A dermoscopic close-up of a skin lesion. The subject is a male aged 28-32.
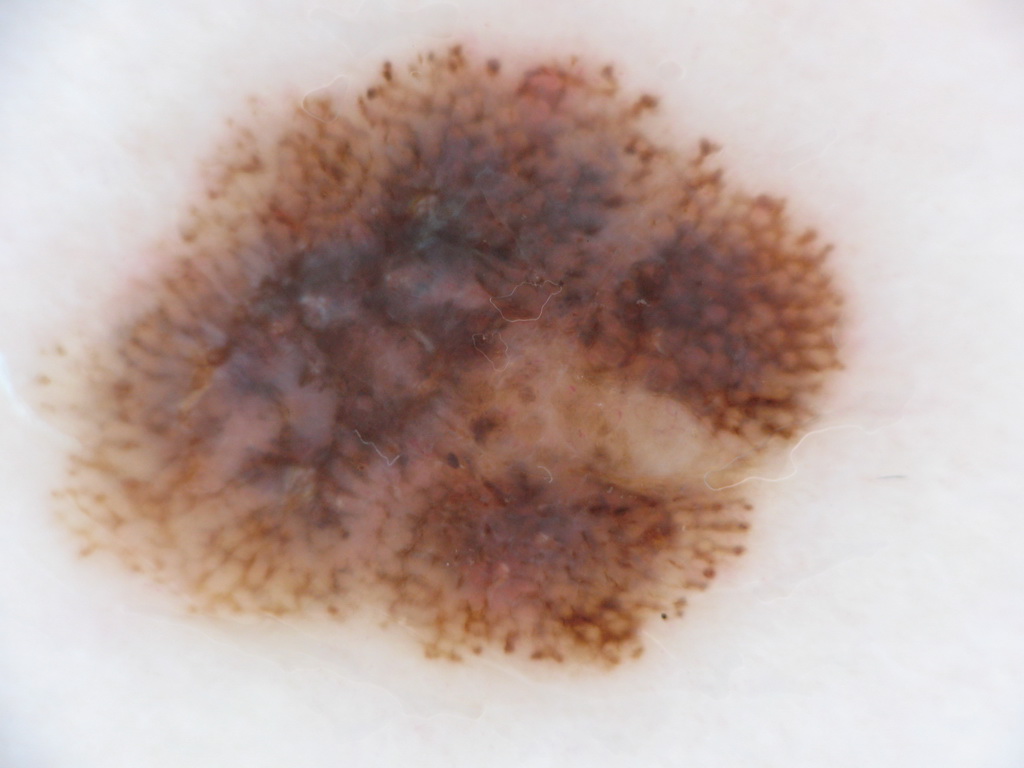| feature | finding |
|---|---|
| dermoscopic pattern | globules, pigment network, and streaks |
| lesion bbox | 34, 30, 861, 680 |
| extent | large |
| impression | a melanocytic nevus |